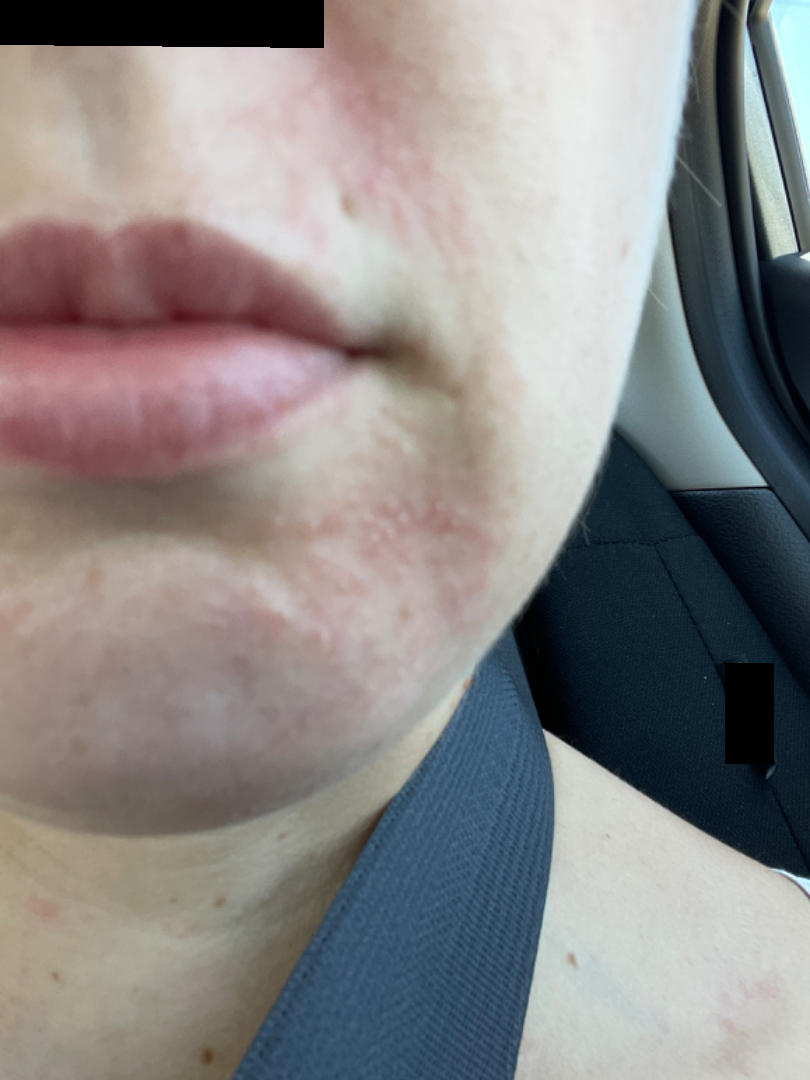* history · one to three months
* contributor · female, age 30–39
* skin tone · Fitzpatrick I; non-clinician graders estimated 2 on the Monk Skin Tone
* photo taken · close-up
* patient's own categorization · a rash
* symptoms · itching
* surface texture · rough or flaky
* impression · Perioral Dermatitis (considered); Seborrheic Dermatitis (considered); Rosacea (unlikely)